Close-up view. The contributor is a male aged 18–29. The lesion involves the back of the torso: 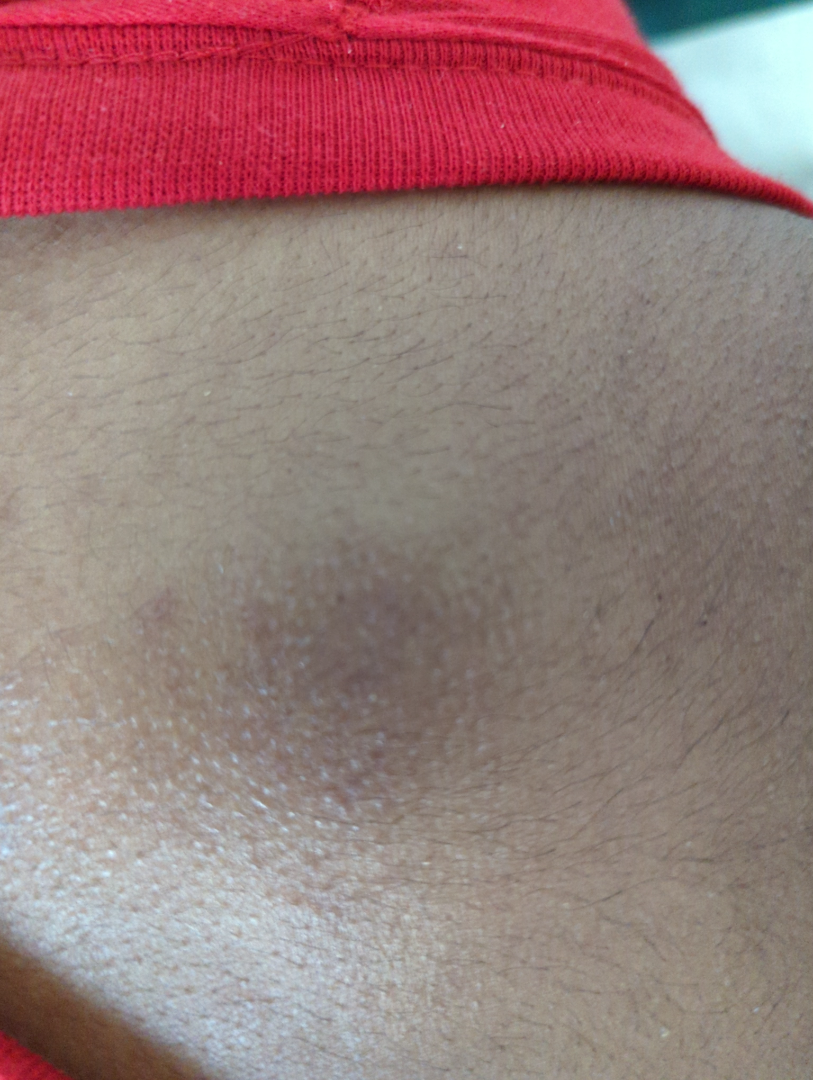The patient reports the condition has been present for one to three months.
Symptoms reported: itching and burning.
No constitutional symptoms were reported.
On teledermatology review, the impression on review was Lichen Simplex Chronicus.